The lesion involves the leg; the subject is female; the photo was captured at an angle.
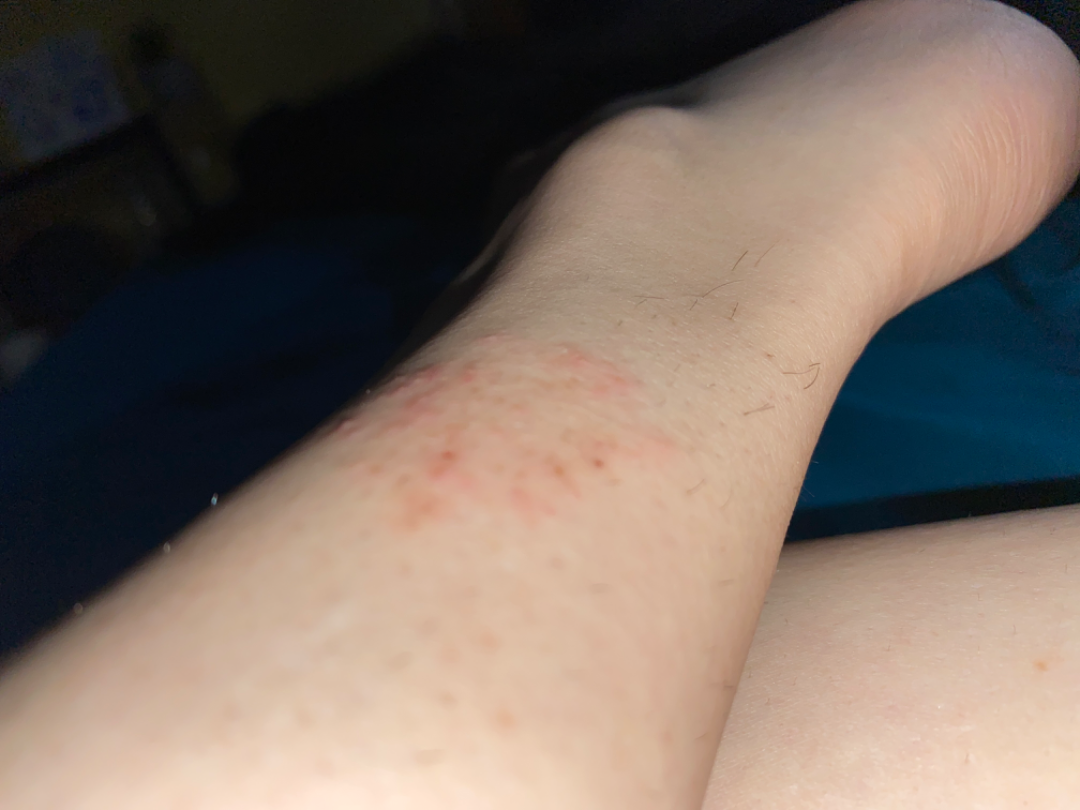self-categorized as = a rash, duration = less than one week, texture = raised or bumpy, differential = Eczema (weight 0.67); Contact dermatitis (weight 0.33).